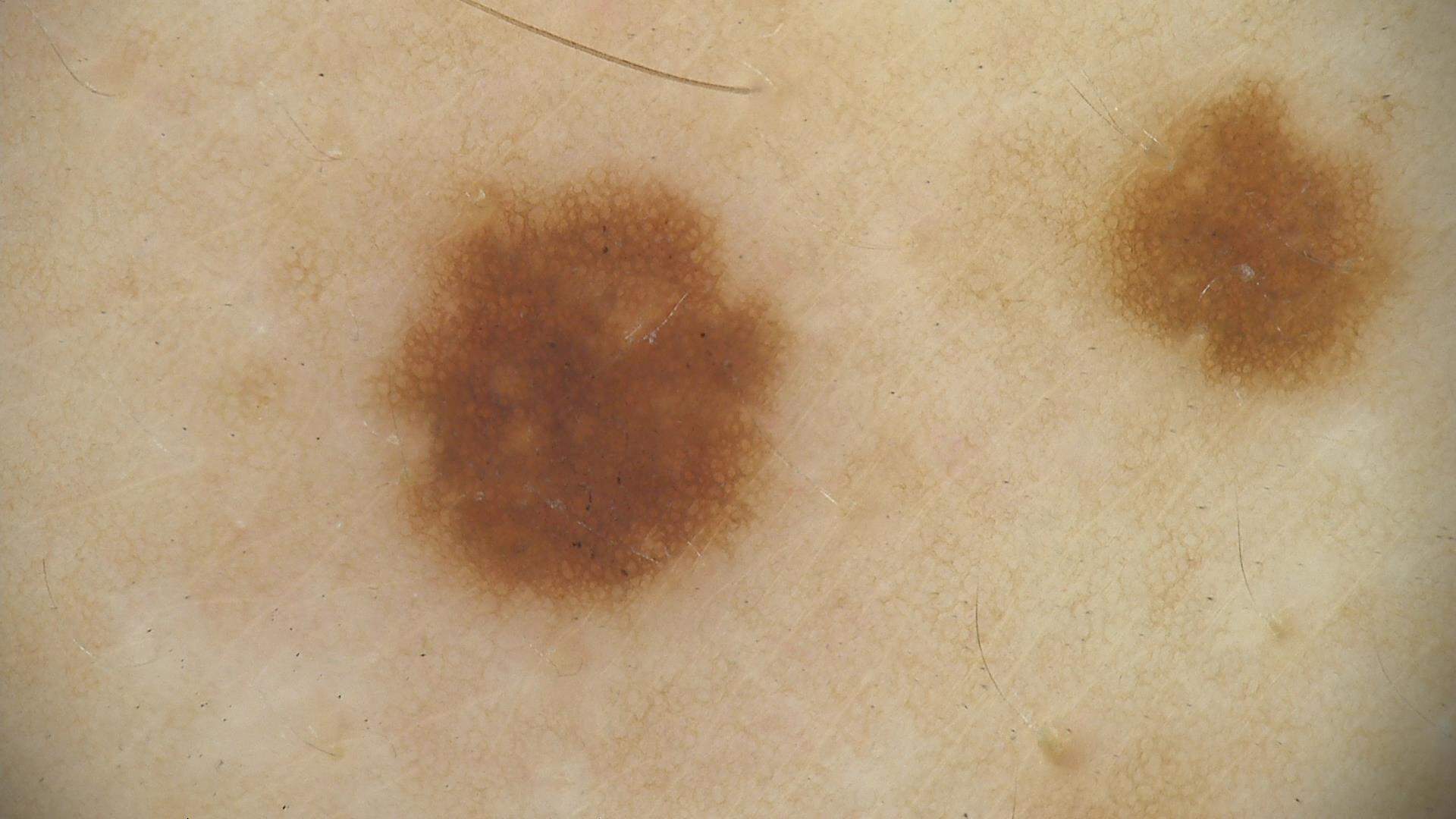Q: What was the diagnostic impression?
A: dysplastic junctional nevus (expert consensus)